A dermoscopic image of a skin lesion: 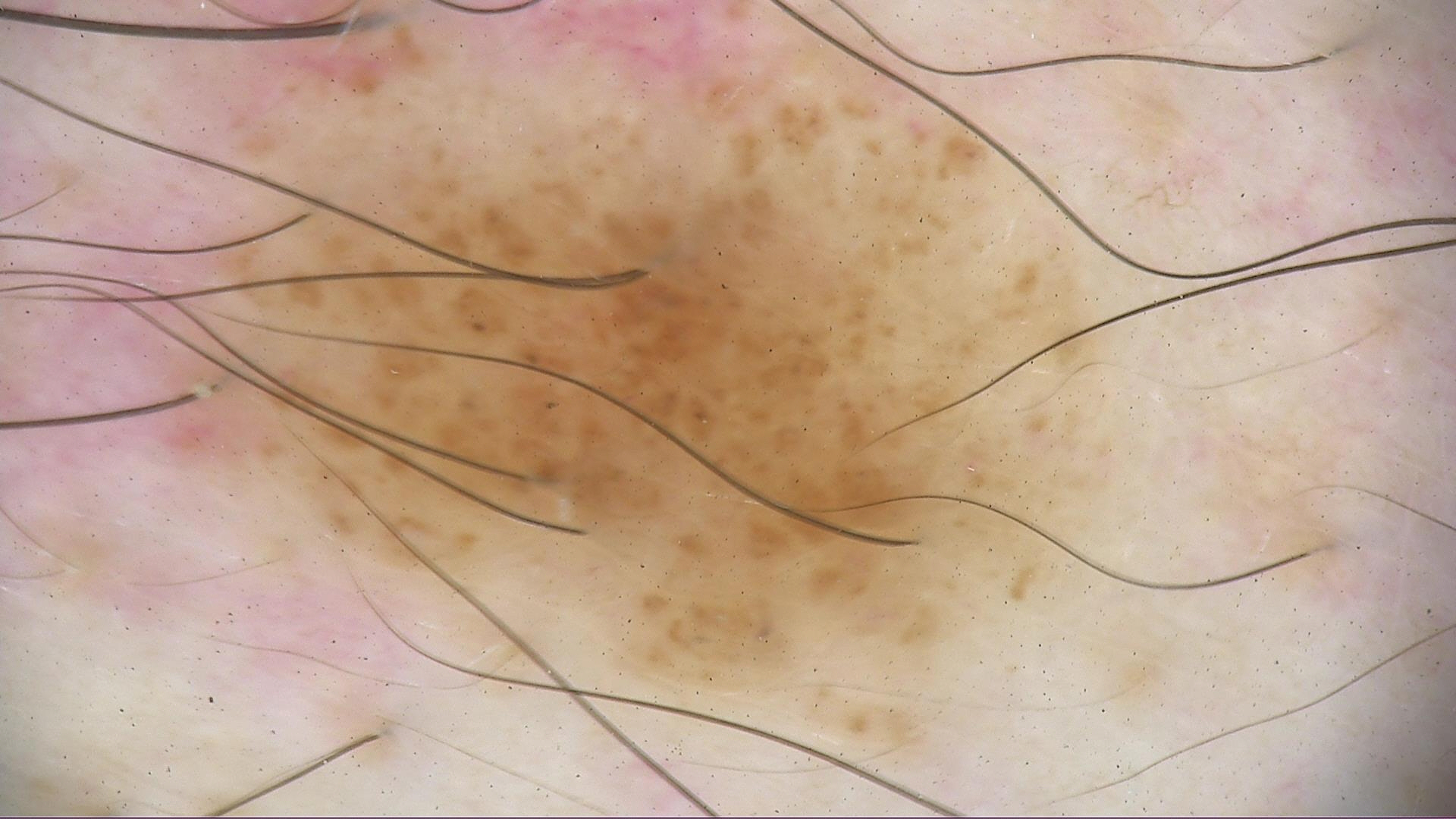lesion type=banal
assessment=compound nevus (expert consensus)